The patient was assessed as FST II · a male subject 87 years old · a clinical close-up photograph of a skin lesion — 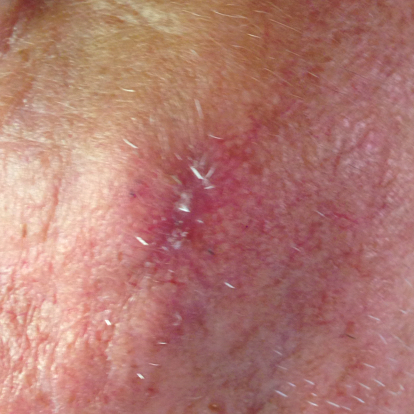Q: What is the anatomic site?
A: the face
Q: What are the lesion's dimensions?
A: 15 × 10 mm
Q: What symptoms does the patient report?
A: pain, bleeding, itching, growth, elevation
Q: What is the diagnosis?
A: basal cell carcinoma (biopsy-proven)